A dermoscopic close-up of a skin lesion.
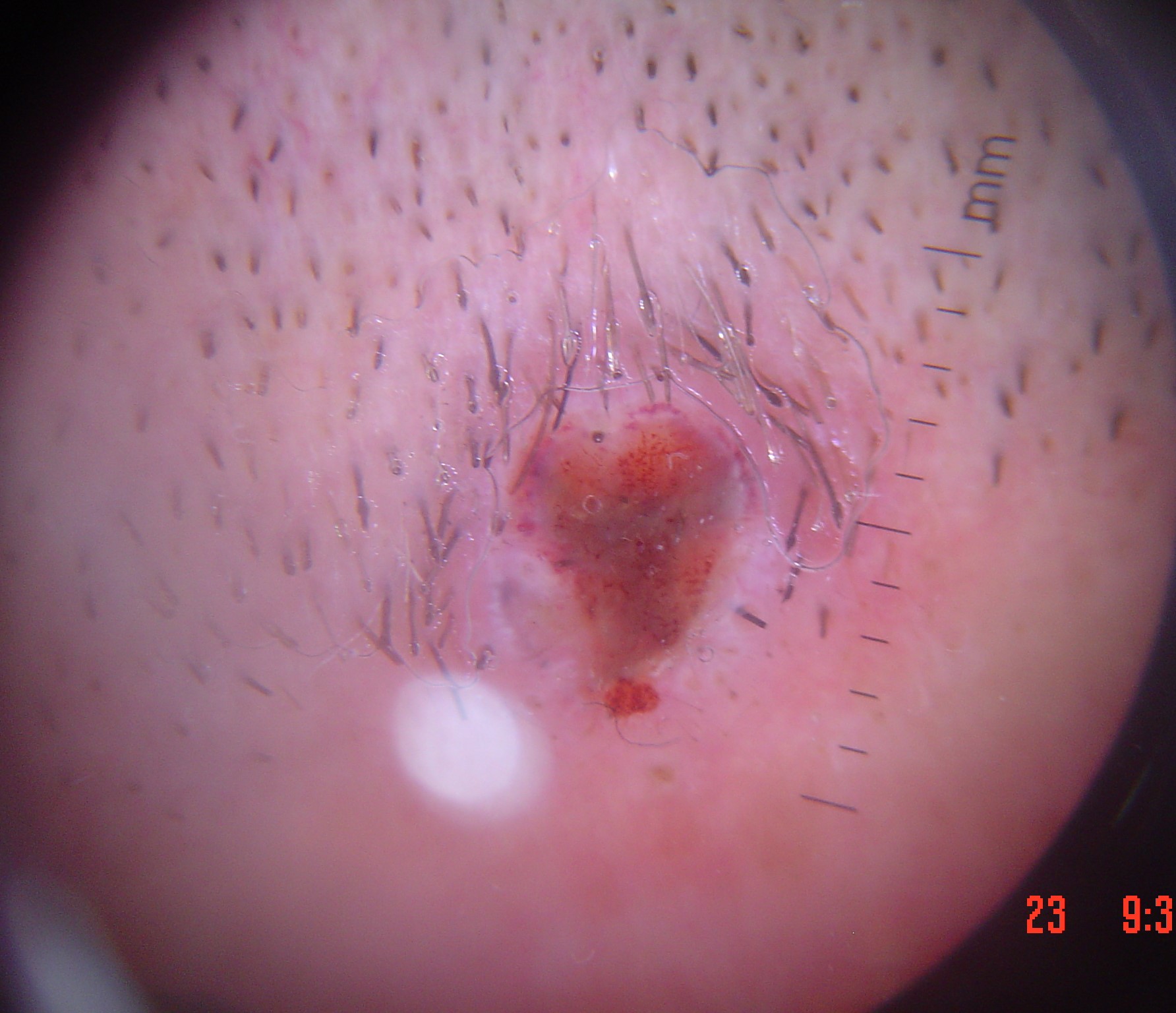The morphology is that of a keratinocytic lesion.
Confirmed on histopathology as a squamous cell carcinoma.